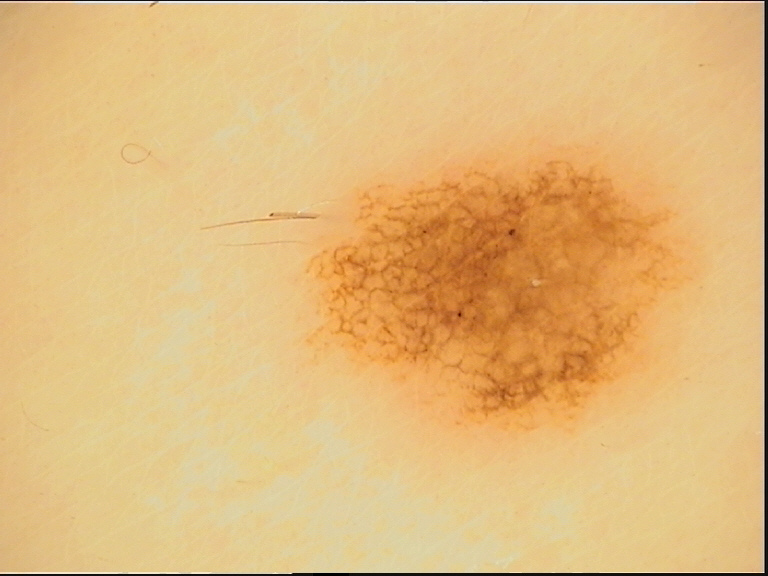A dermoscopic close-up of a skin lesion.
Consistent with a dysplastic junctional nevus.